A dermatoscopic image of a skin lesion:
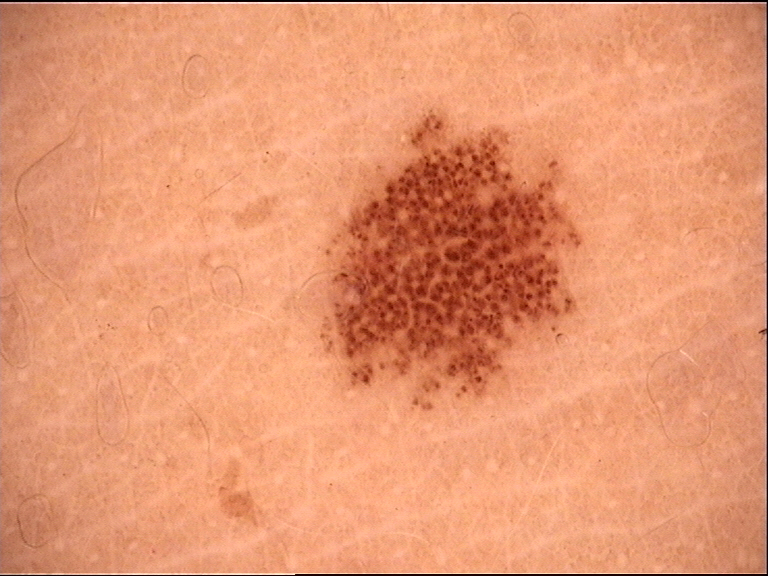Classified as a benign lesion — a dysplastic junctional nevus.